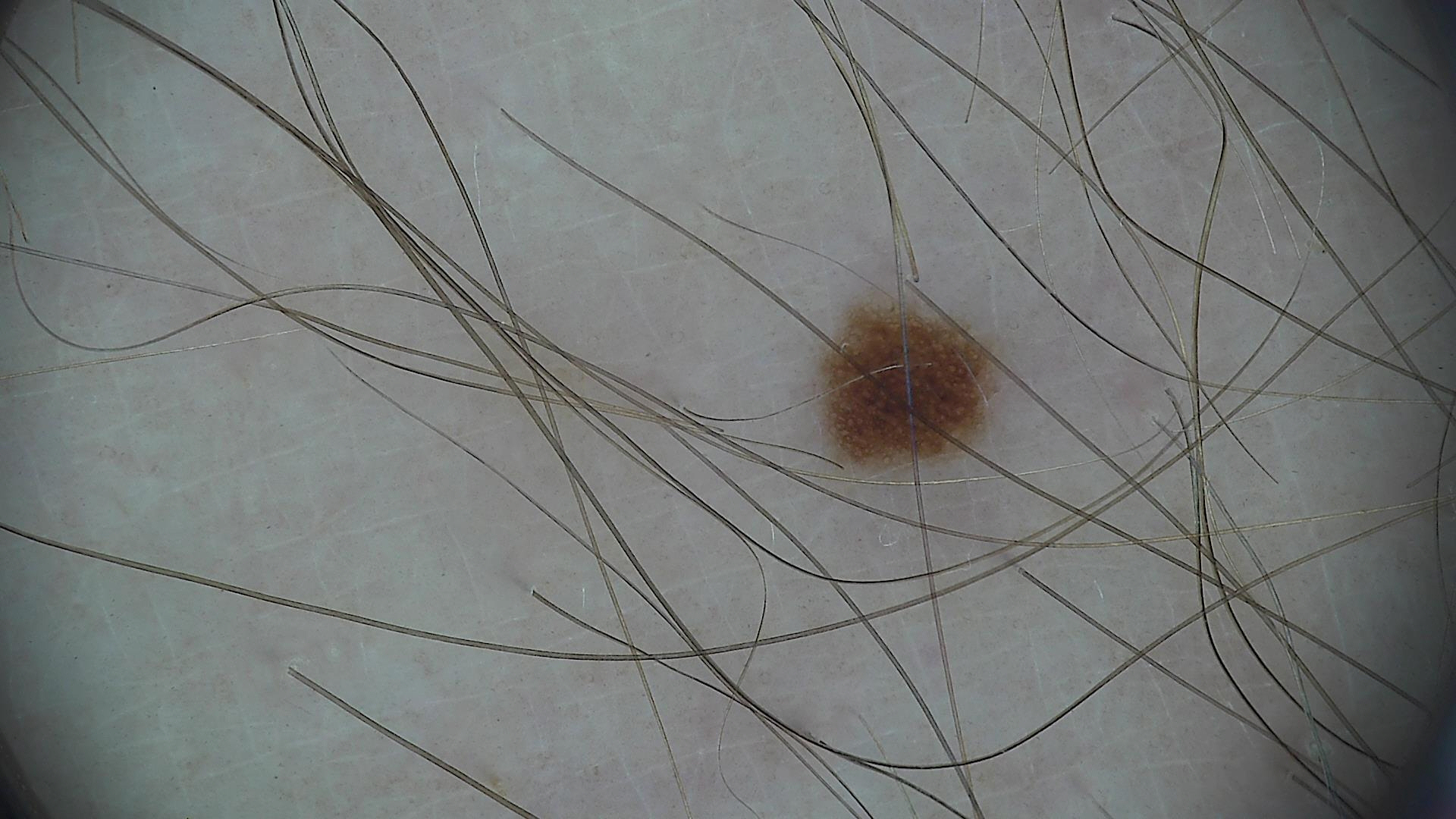{"image": "dermoscopy", "lesion_type": {"main_class": "banal", "pattern": "junctional"}, "diagnosis": {"name": "junctional nevus", "code": "jb", "malignancy": "benign", "super_class": "melanocytic", "confirmation": "expert consensus"}}